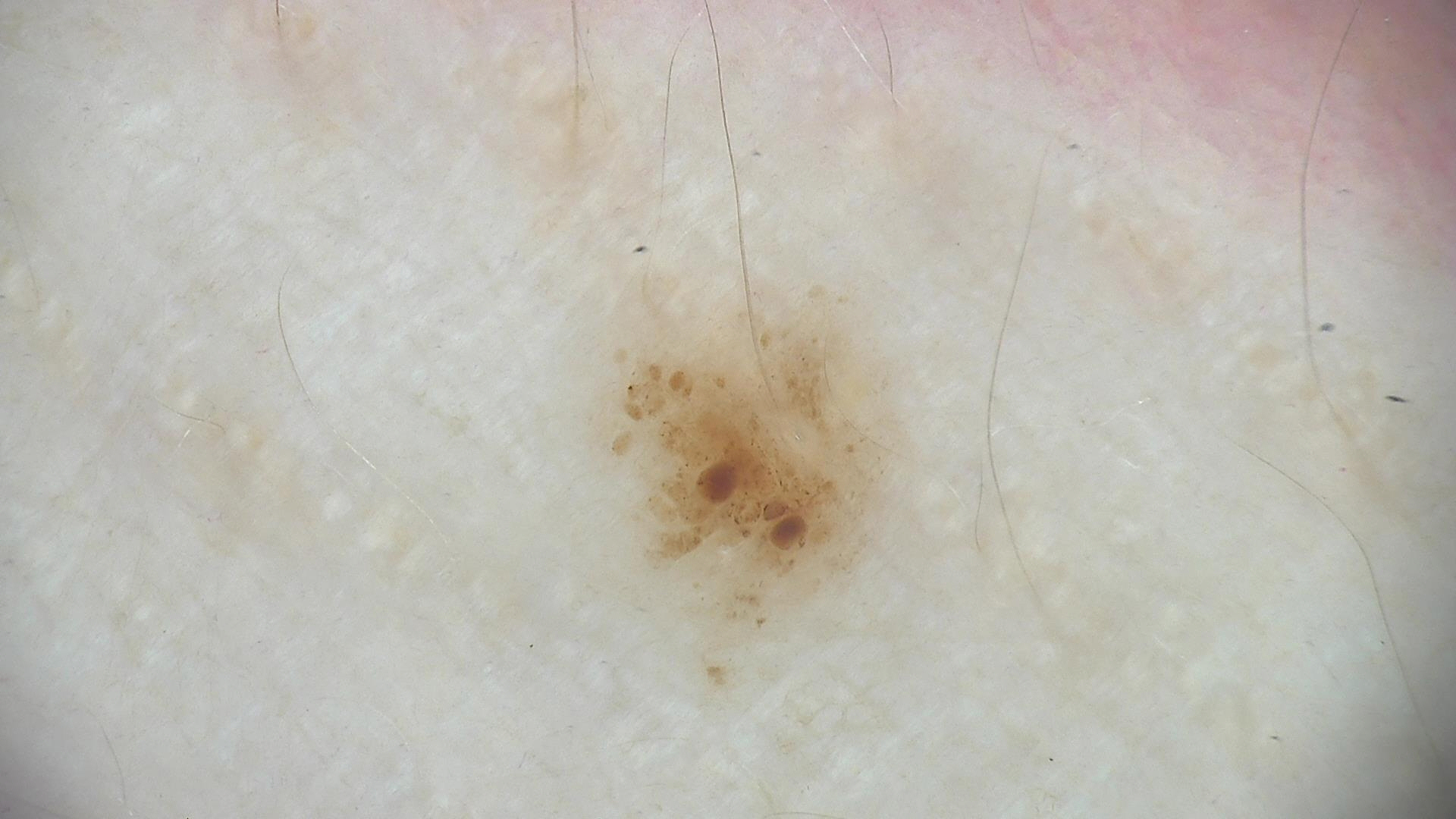A skin lesion imaged with a dermatoscope. Labeled as a dysplastic junctional nevus.